A dermoscopic close-up of a skin lesion: 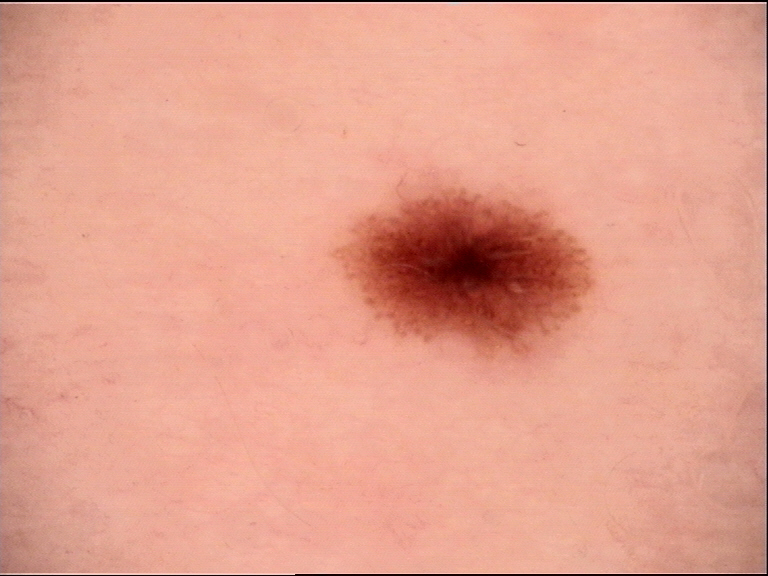Q: What is the diagnosis?
A: dysplastic junctional nevus (expert consensus)